The affected area is the front of the torso, head or neck, palm, arm, back of the torso, back of the hand, top or side of the foot, leg and sole of the foot; the photograph is a close-up of the affected area: 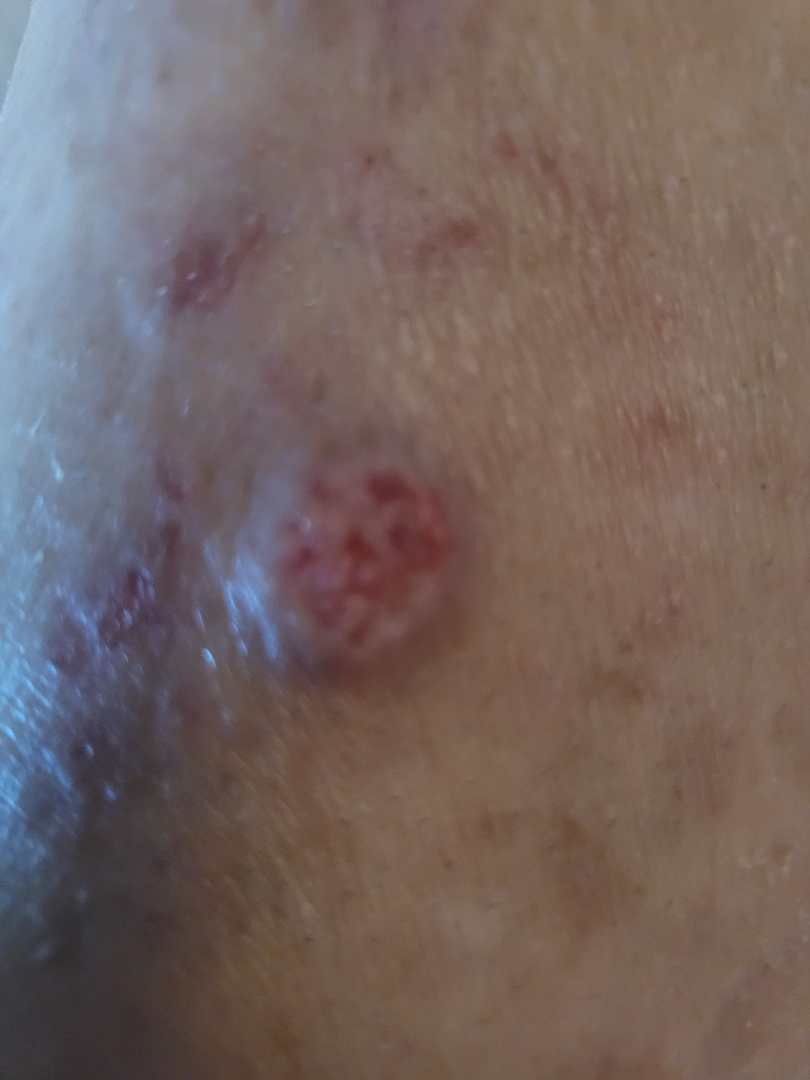{
  "assessment": "indeterminate"
}